The patient is 50–59, female; texture is reported as raised or bumpy; the condition has been present for three to twelve months; the photo was captured at an angle; no associated systemic symptoms reported; reported lesion symptoms include enlargement, bothersome appearance and itching; the lesion involves the leg; the patient described the issue as a rash: 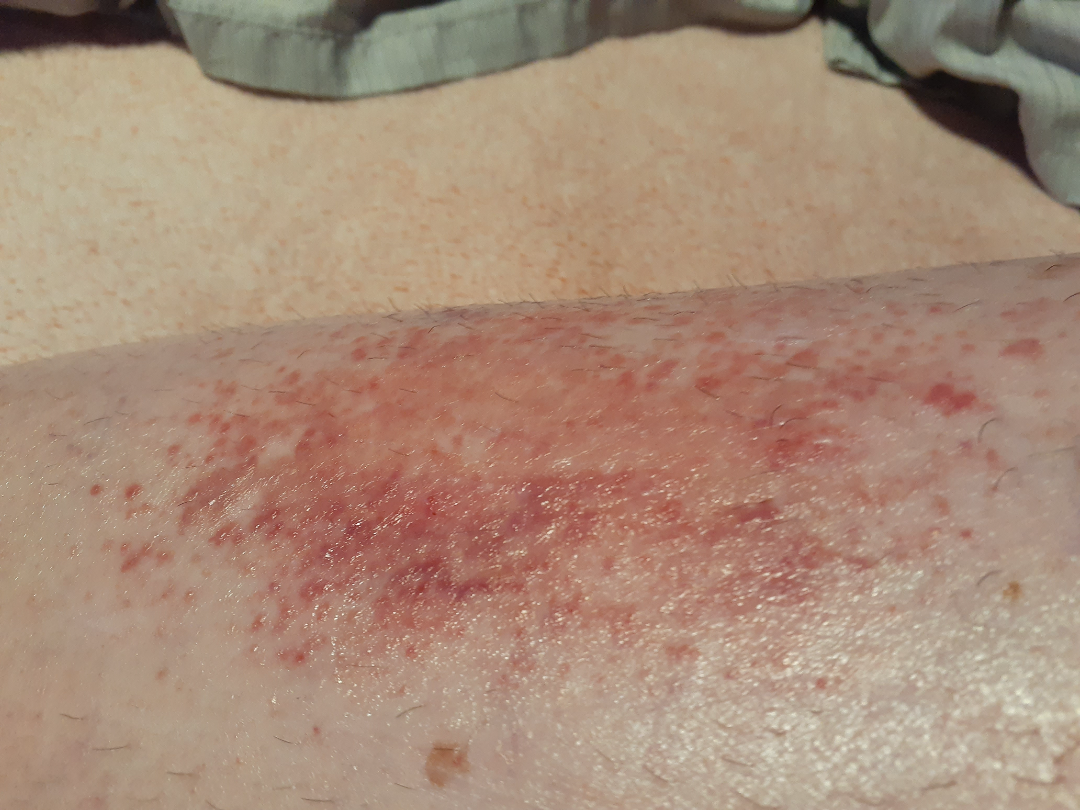* diagnostic considerations · the leading impression is Allergic Contact Dermatitis; lower on the differential is Eczema; less probable is Stasis Dermatitis; less likely is Burn of skin; a more distant consideration is Acute dermatitis, NOS; a remote consideration is Irritant Contact Dermatitis; less probable is Pretibial myxedema